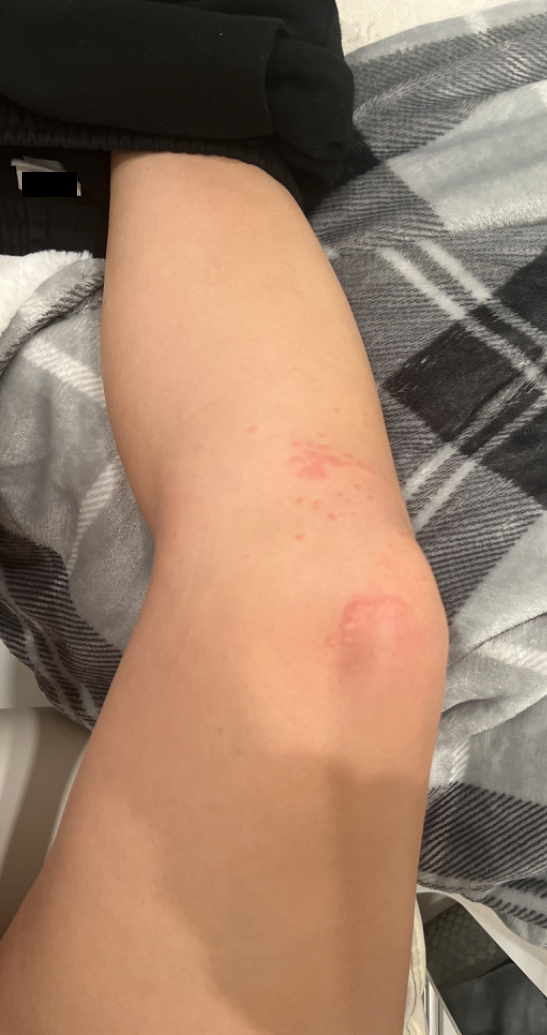<report>
  <assessment>unable to determine</assessment>
</report>